A dermoscopy image of a single skin lesion.
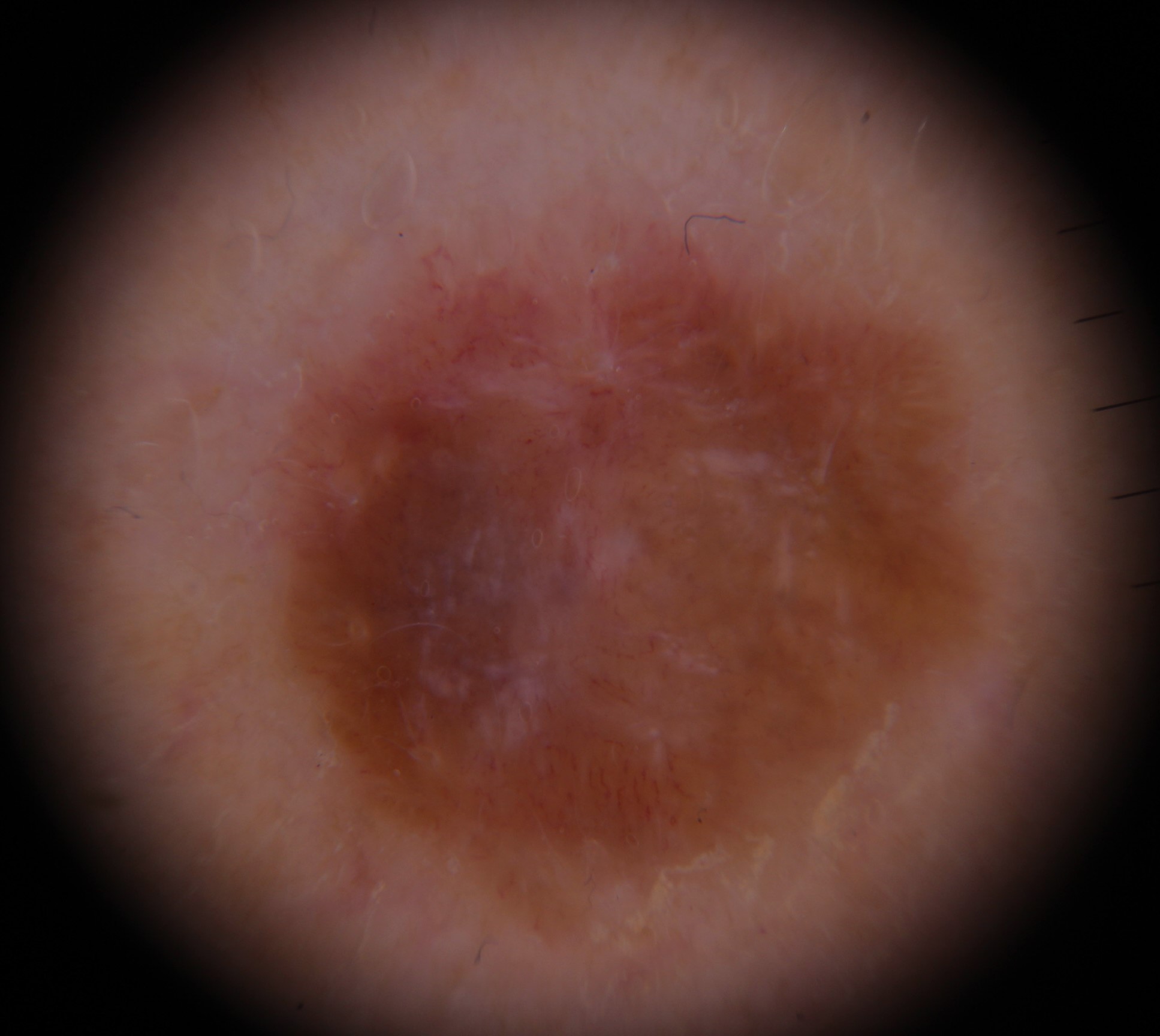Q: What is the diagnosis?
A: melanoma (biopsy-proven)